Dermoscopy of a skin lesion:
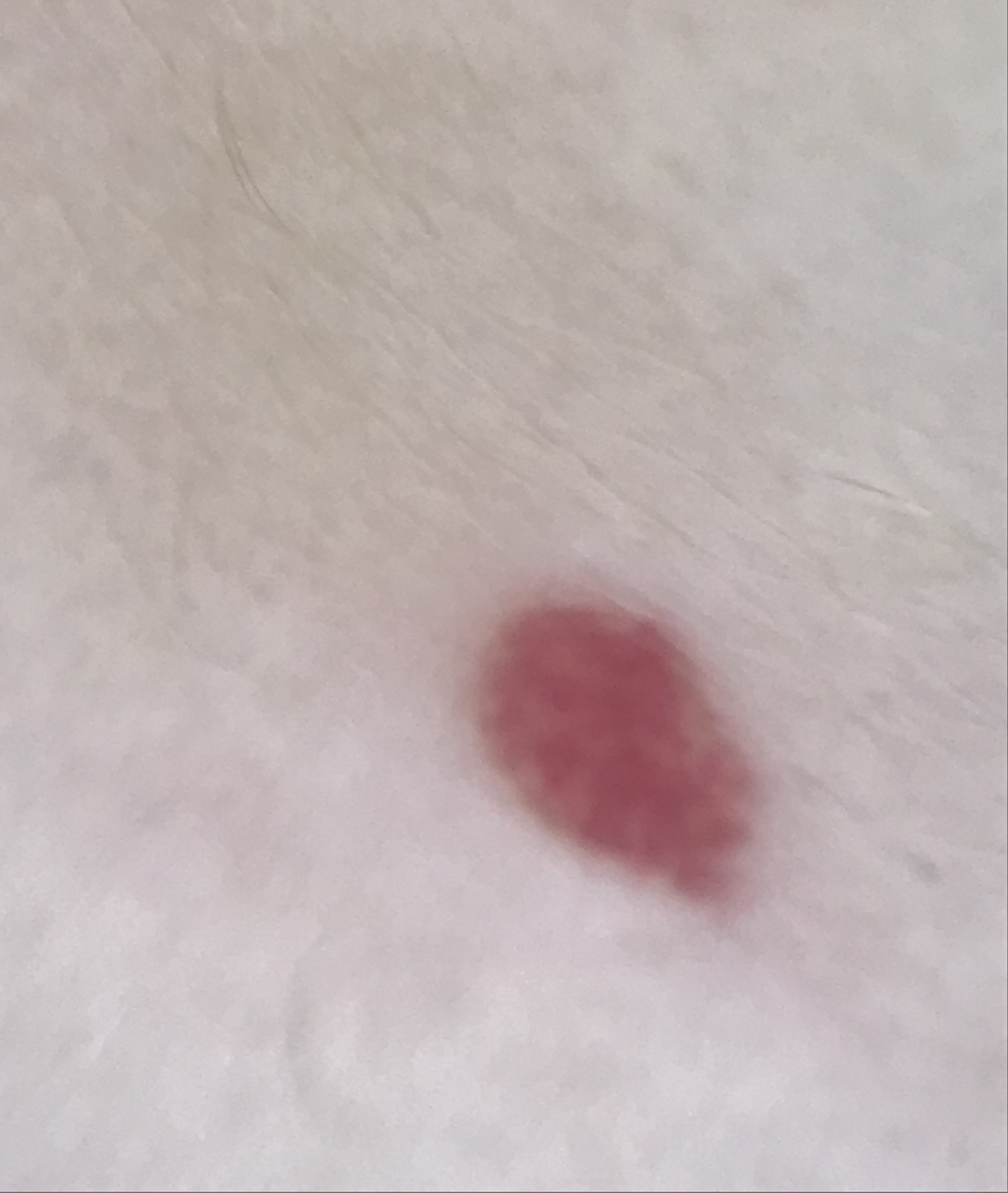Labeled as a hemangioma.